Located on the leg · the photograph is a close-up of the affected area · the subject is 50–59, female.
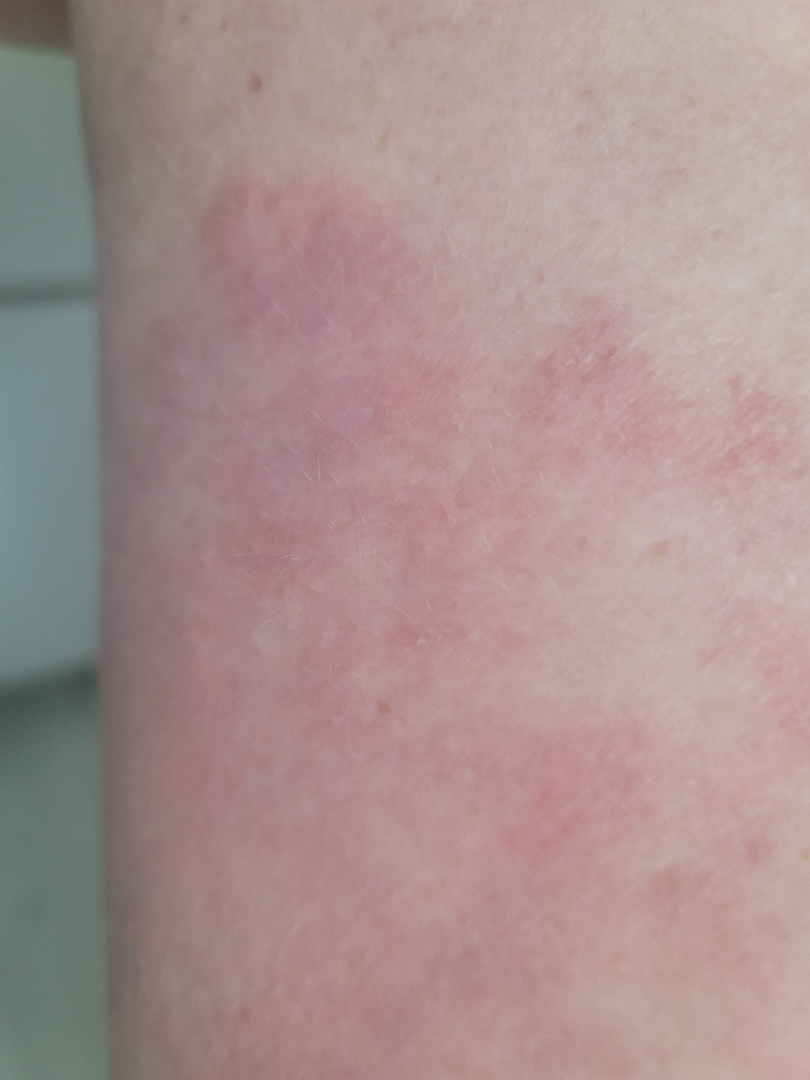• onset — three to twelve months
• lesion texture — raised or bumpy and rough or flaky
• patient's own categorization — a rash
• skin tone — Fitzpatrick III
• clinical impression — Hypersensitivity (considered); Allergic Contact Dermatitis (considered); Erythema migrans (considered)